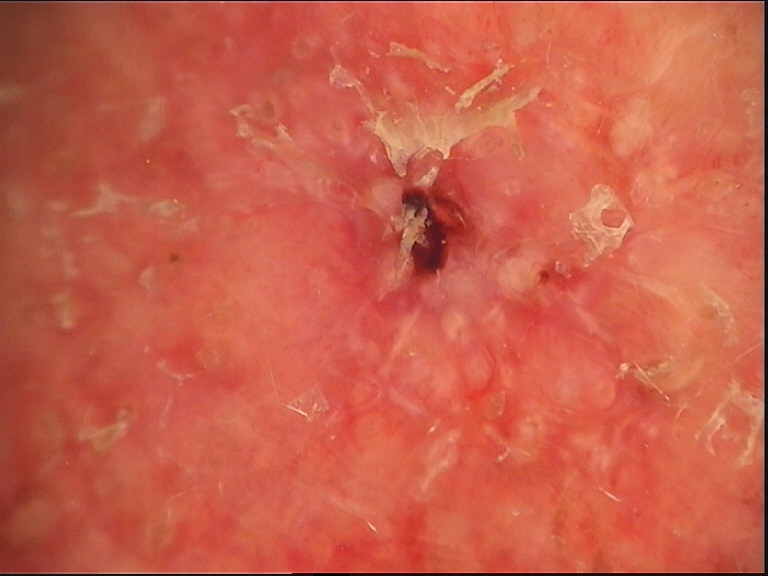The architecture is that of a keratinocytic lesion.
Histopathologically confirmed as a basal cell carcinoma.